Dermoscopy of a skin lesion: 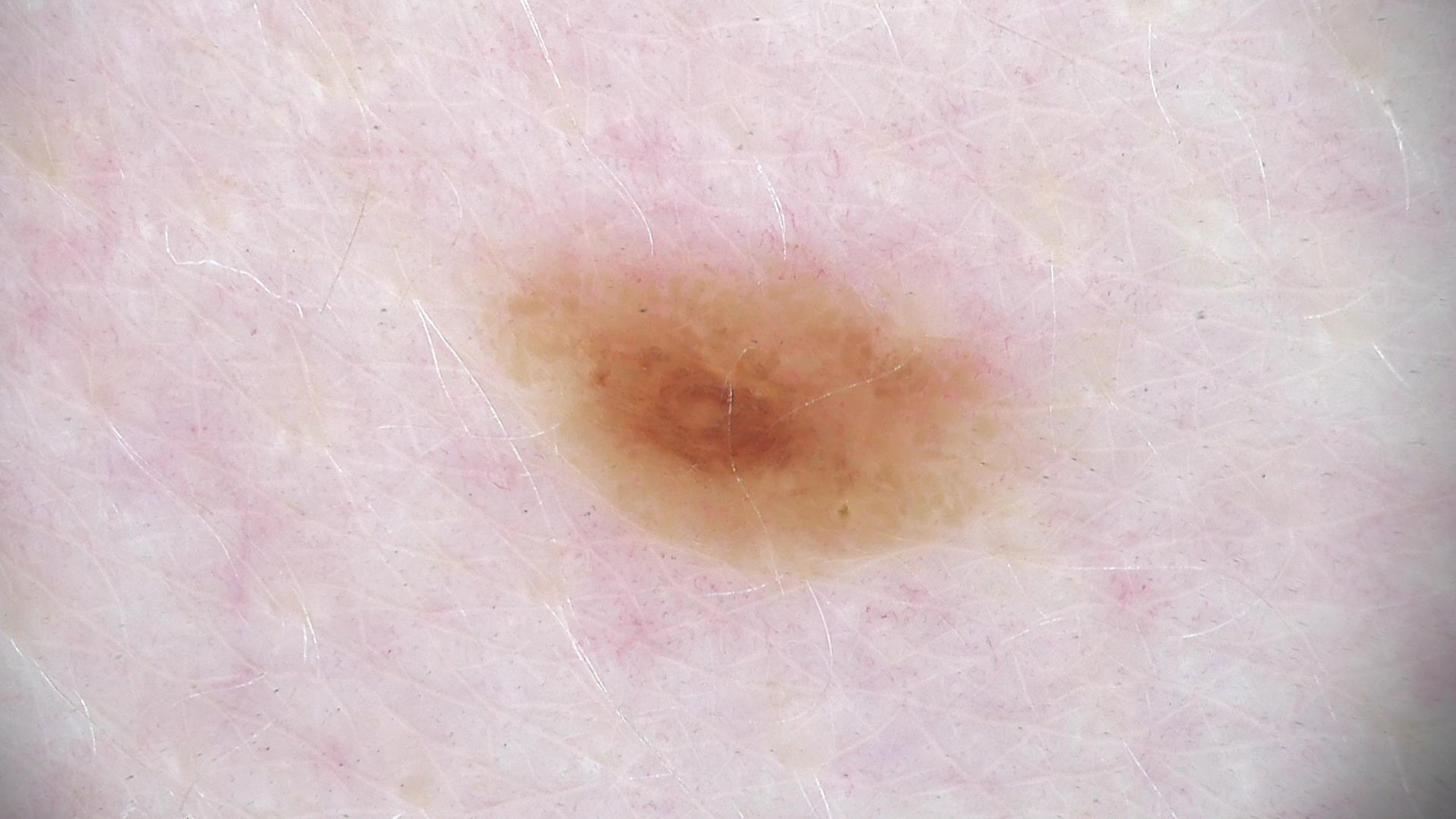class: dysplastic junctional nevus (expert consensus)